A female subject aged approximately 45 · a skin lesion imaged with contact-polarized dermoscopy:
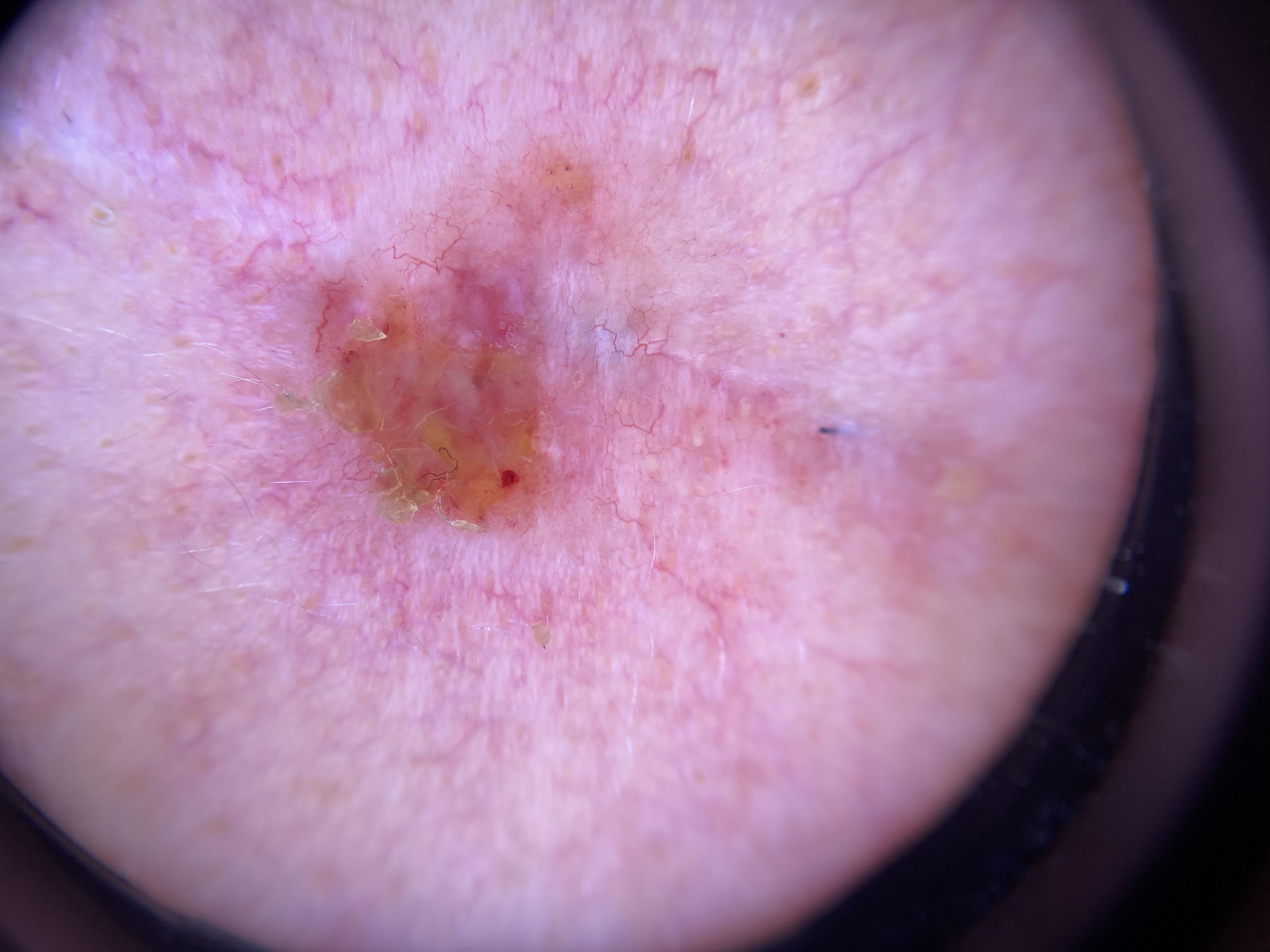The lesion was found on the head or neck. The biopsy diagnosis was a tumor of follicular differentiation — a basal cell carcinoma.